A skin lesion imaged with a dermatoscope — 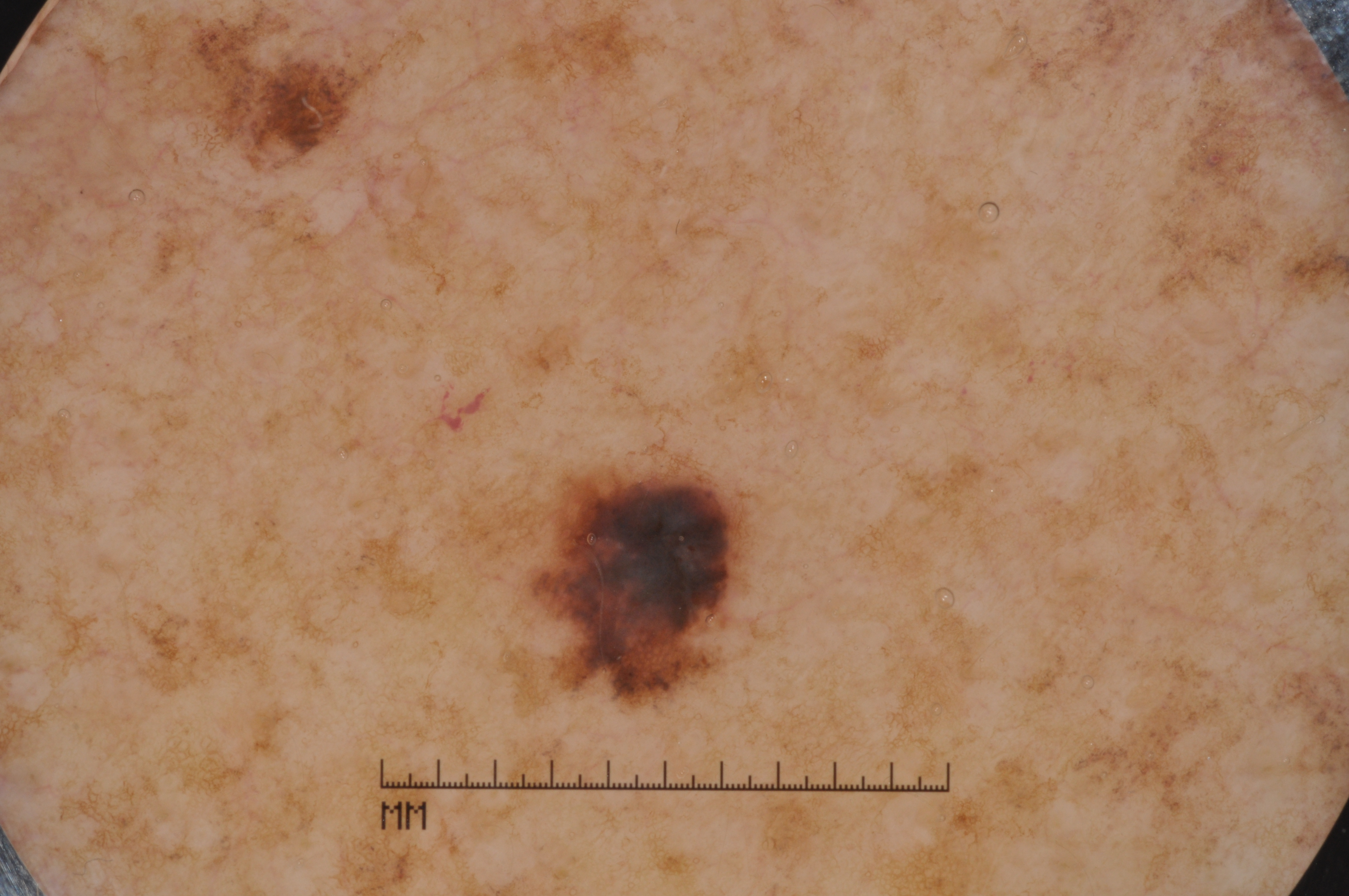Q: How large is the lesion within the image?
A: ~3% of the field
Q: Where is the lesion in the image?
A: box(523, 453, 758, 714)
Q: What dermoscopic features are present?
A: pigment network; absent: negative network, milia-like cysts, and streaks
Q: What did the assessment conclude?
A: a melanoma